A skin lesion imaged with a dermatoscope:
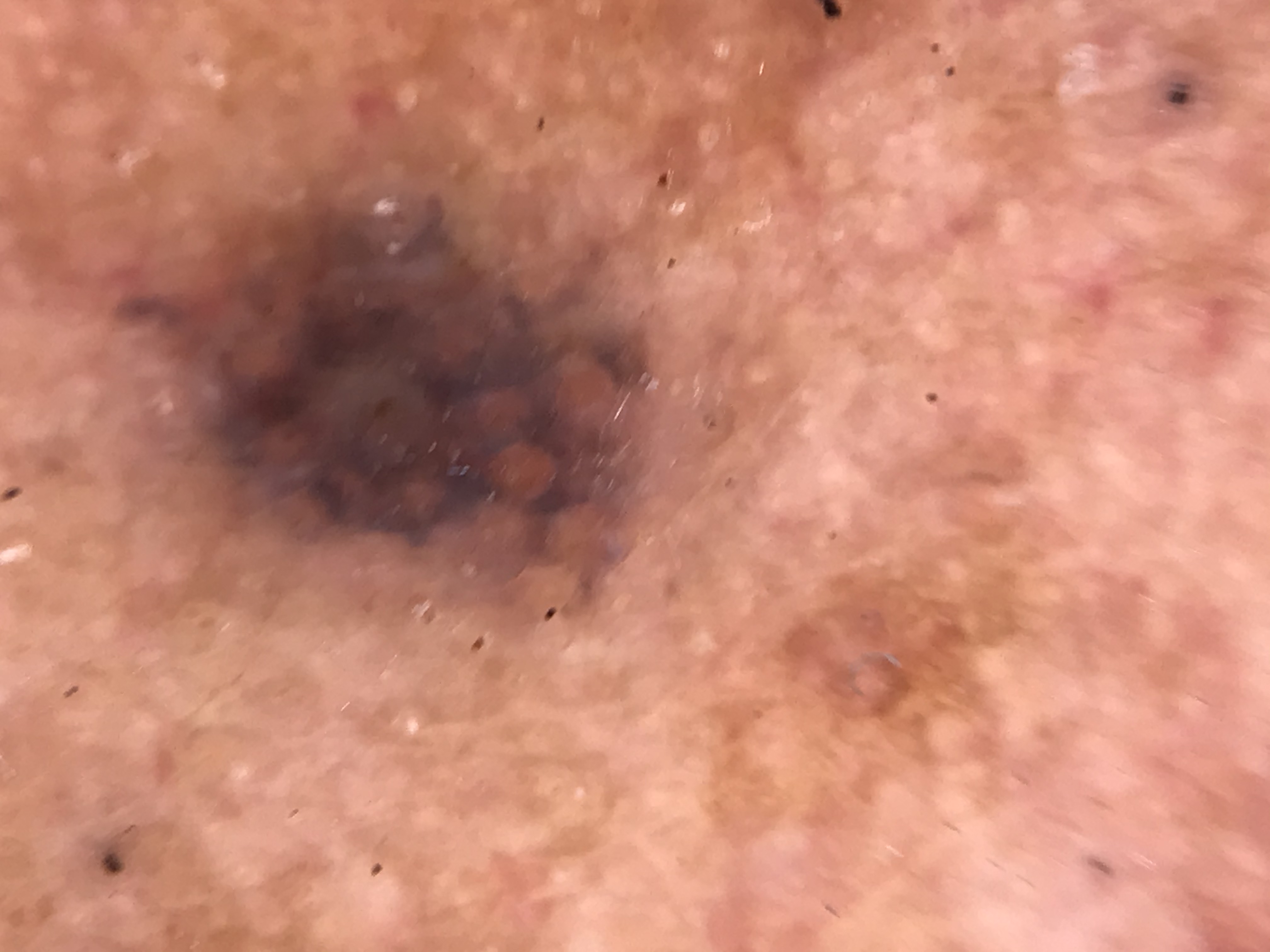diagnosis: Miescher nevus (expert consensus).